The subject is a male aged around 50; a dermoscopic view of a skin lesion:
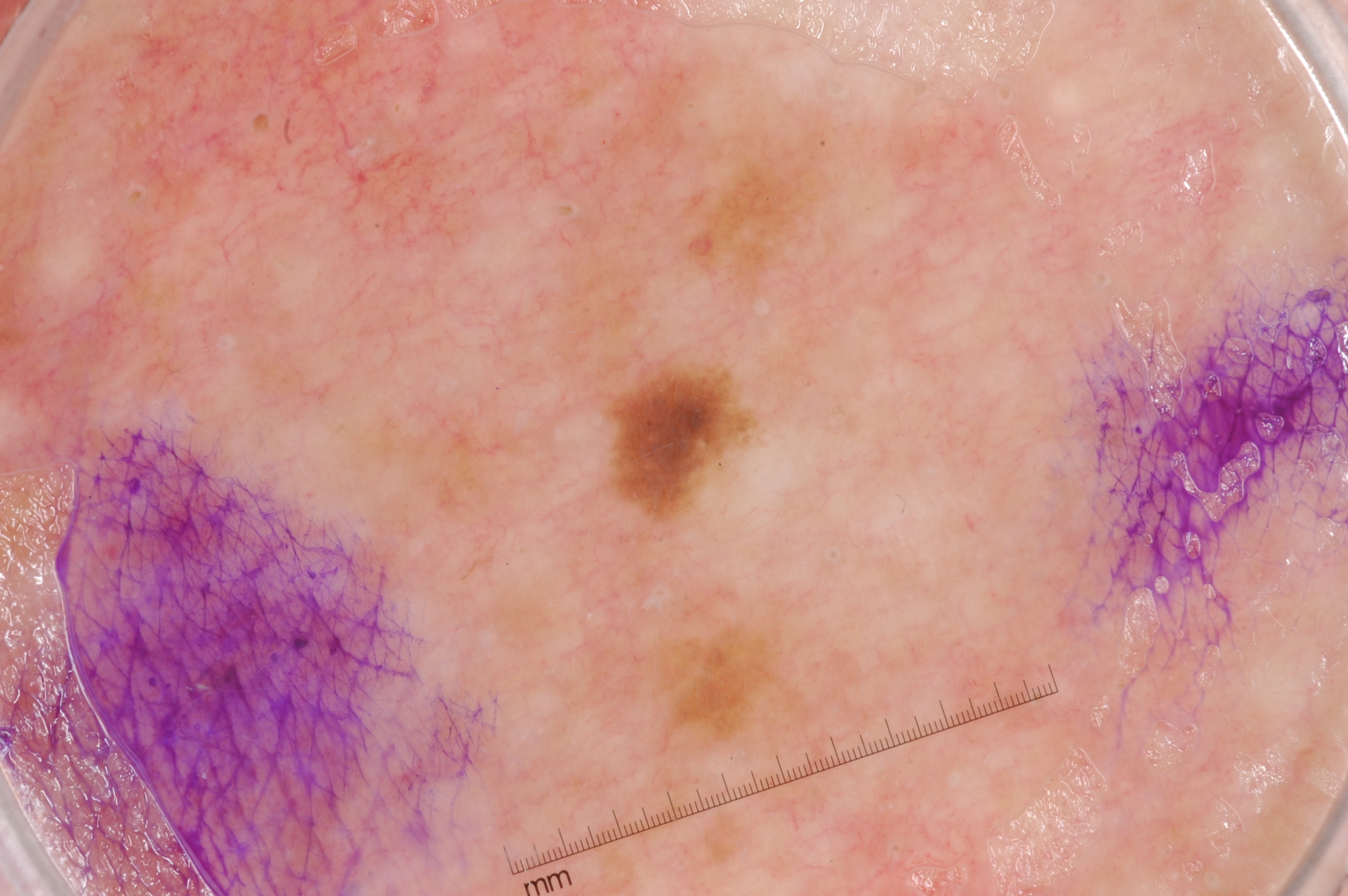Dermoscopically, the lesion shows no streaks, milia-like cysts, negative network, or pigment network.
The lesion covers approximately 2% of the dermoscopic field.
As (left, top, right, bottom), the lesion occupies the region bbox=[597, 357, 770, 525].
Consistent with a melanocytic nevus, a benign skin lesion.